Dermoscopy of a skin lesion, the subject is a female aged around 50: 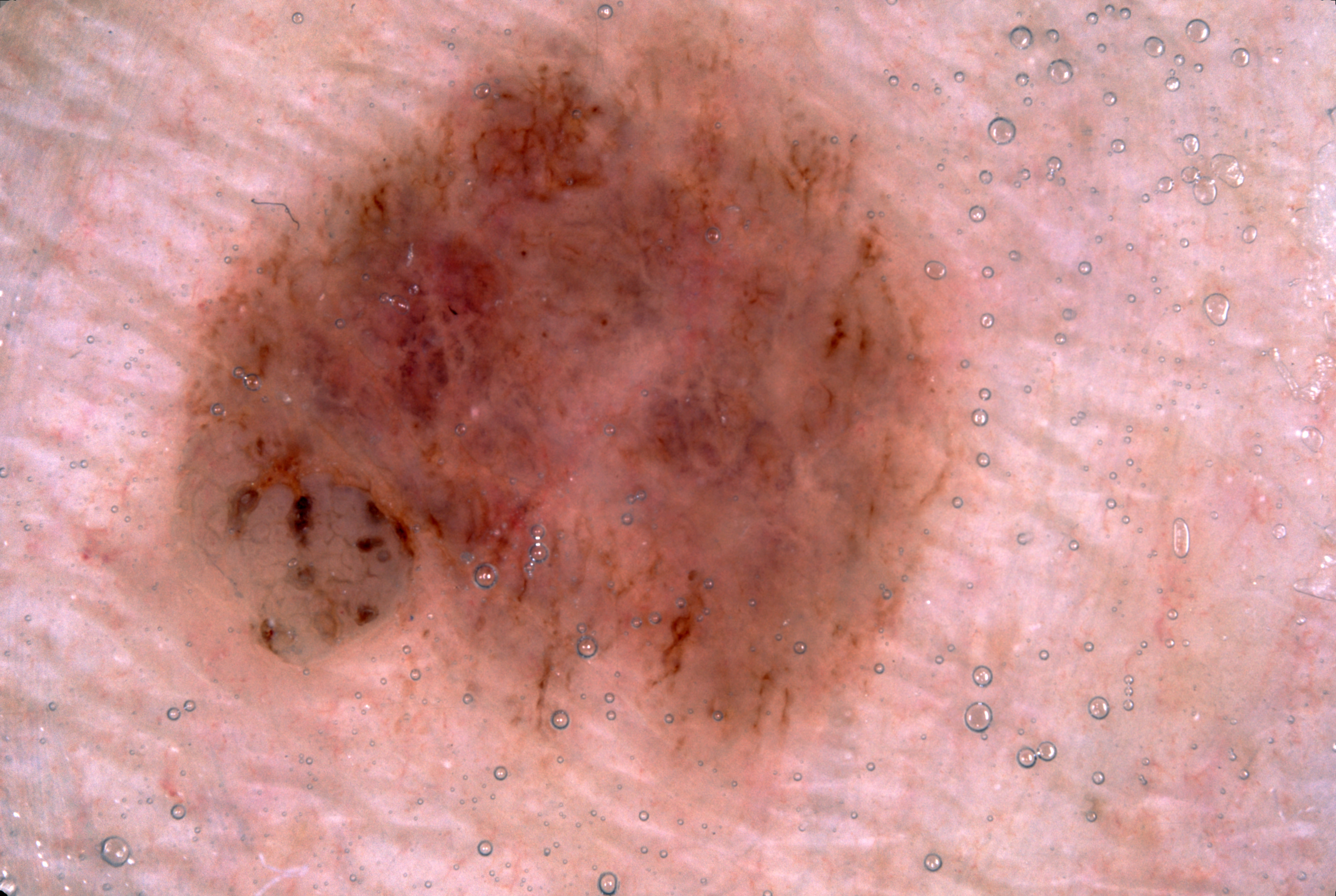dermoscopic features: pigment network
lesion location: <box>79, 0, 989, 828</box>
lesion extent: ~40% of the field
lesion margin: clipped at the frame edge
impression: a melanocytic nevus, a benign skin lesion